The photograph was taken at an angle. The lesion involves the leg, front of the torso, head or neck, back of the torso and arm. The contributor is 50–59, female — 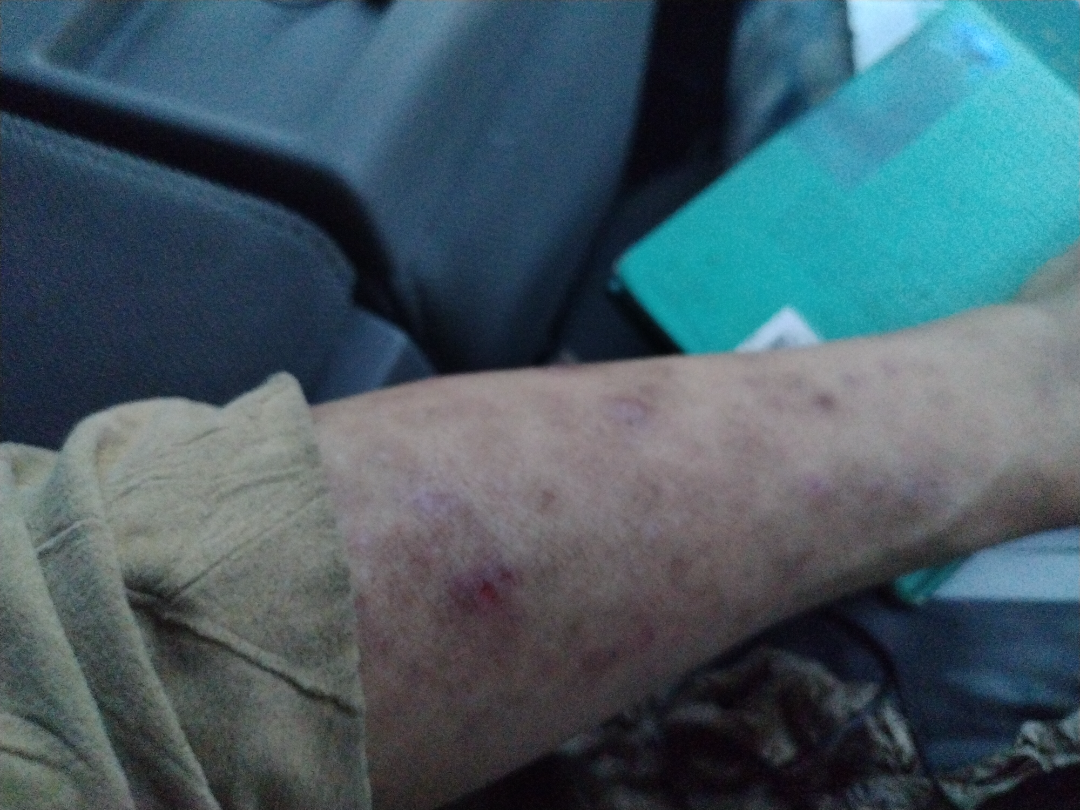Findings:
- differential · the favored diagnosis is Lichen Simplex Chronicus; an alternative is Eczema